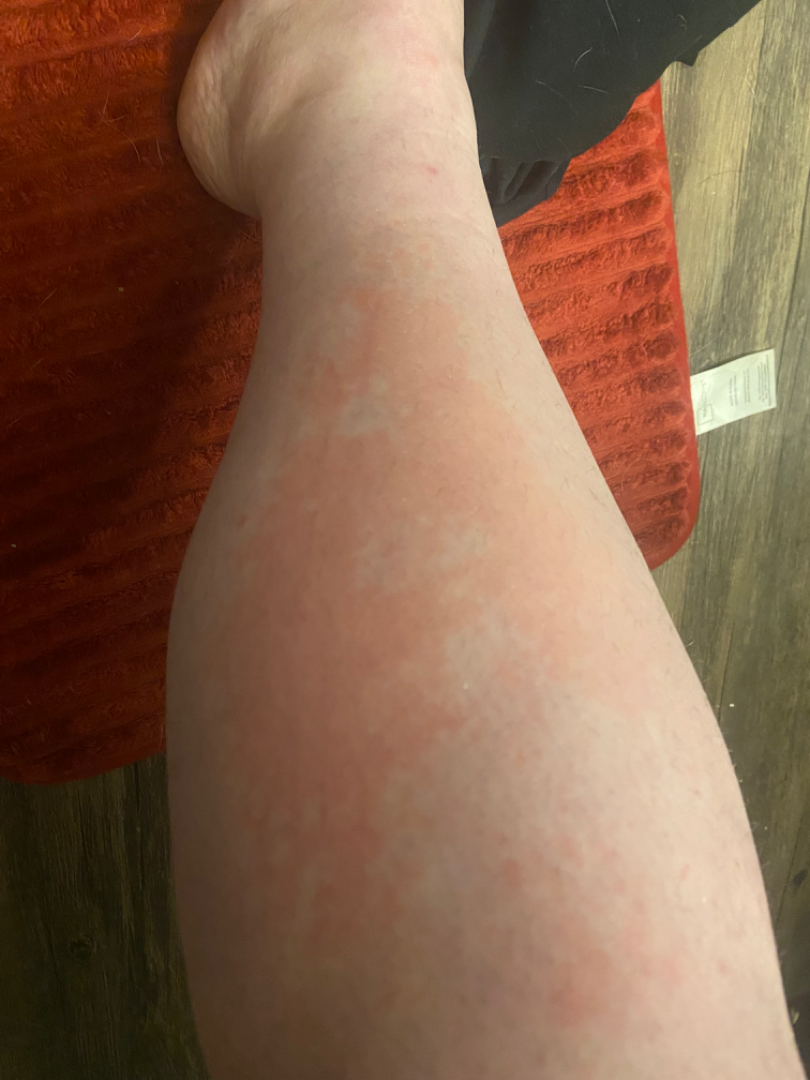The case was difficult to assess from the available photograph.